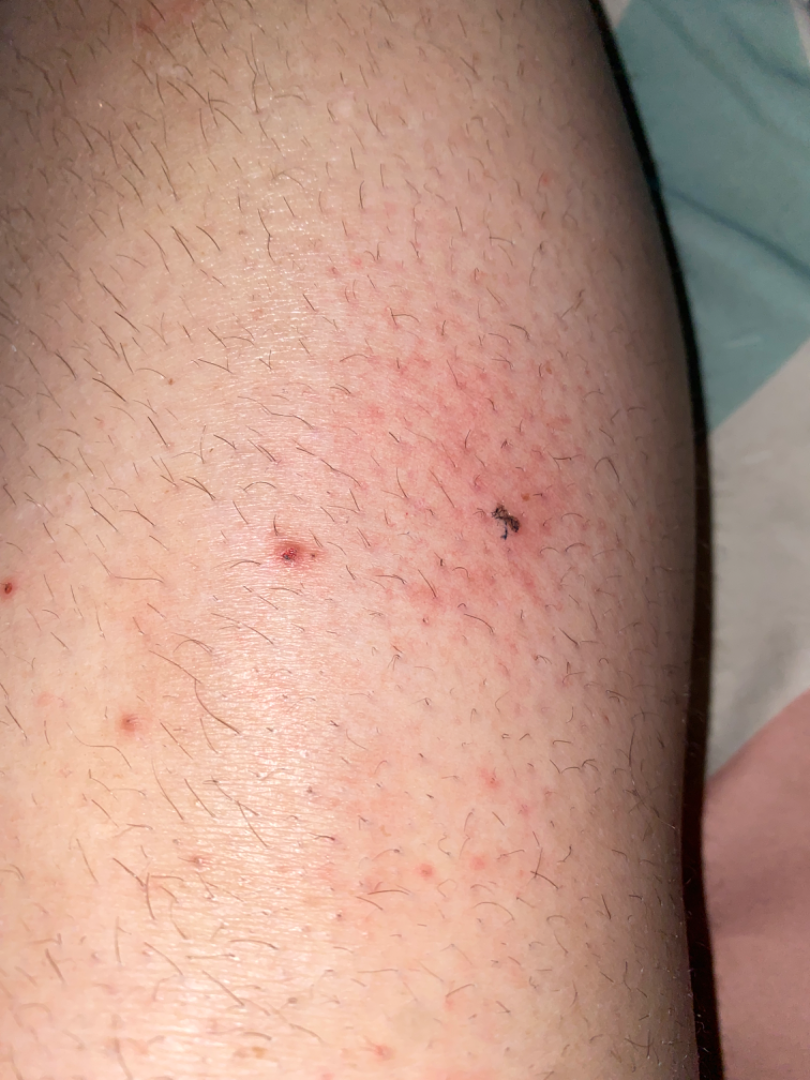Background: Female patient, age 18–29. This is a close-up image. The lesion involves the leg. Findings: The reviewing dermatologists' impression was: Folliculitis (leading); Acute dermatitis, NOS (unlikely); Ingrown hair (unlikely); Insect Bite (unlikely); Infection of tick bite (unlikely); Eczema (unlikely); Hypersensitivity (unlikely).